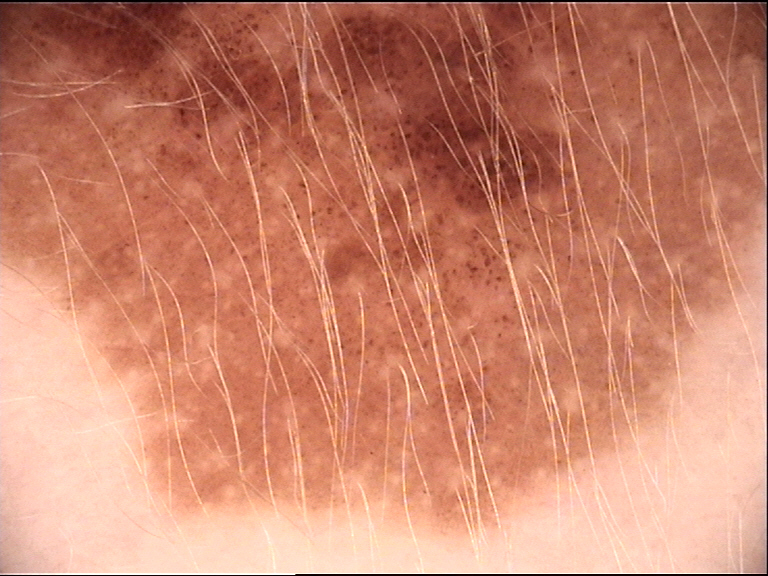The diagnosis was a congenital junctional nevus.